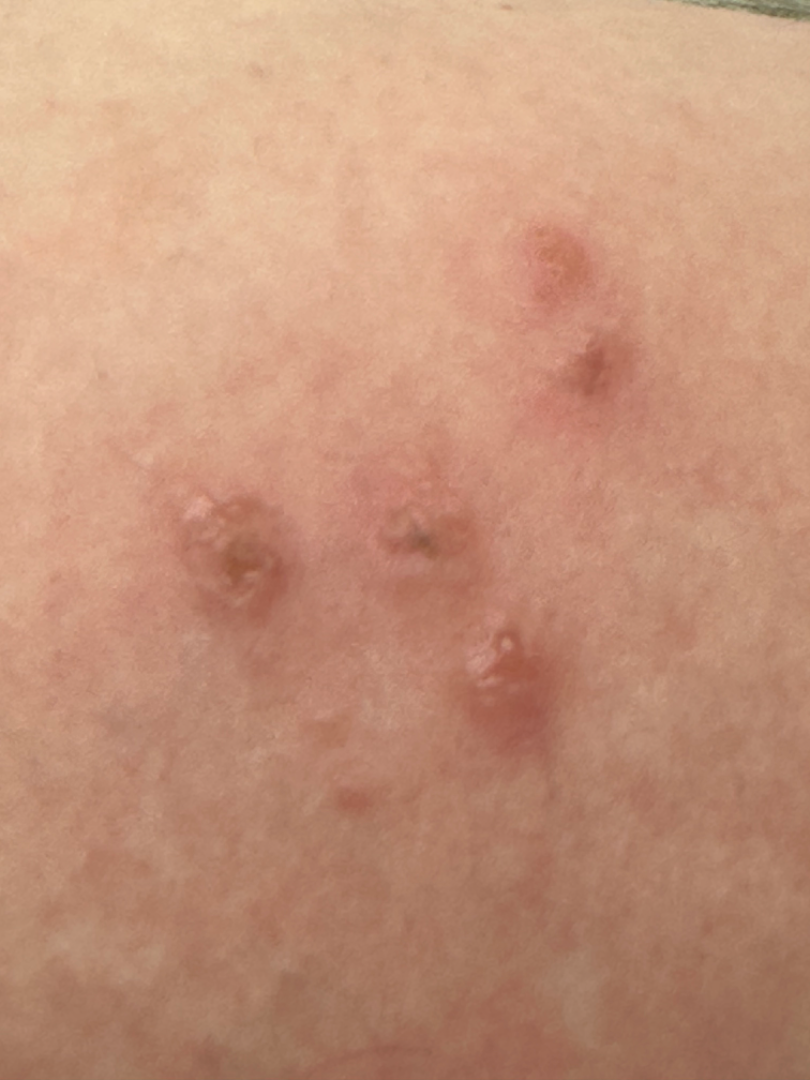assessment: ungradable on photographic review | systemic symptoms: none reported | patient describes the issue as: a rash | body site: leg | photo taken: close-up | contributor: female, age 18–29 | lesion symptoms: bothersome appearance, pain, itching and burning | lesion texture: fluid-filled, raised or bumpy and rough or flaky.